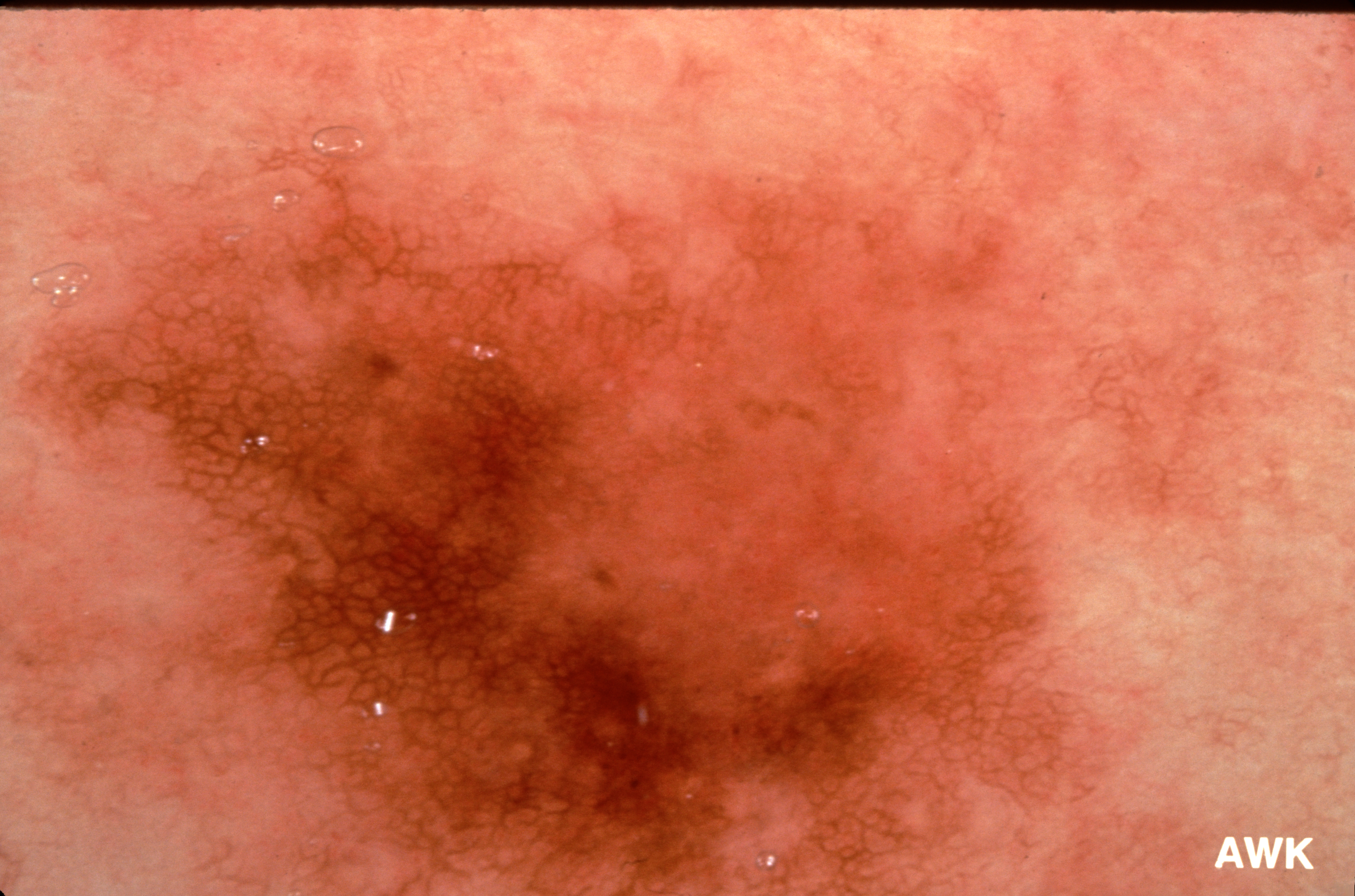A dermatoscopic image of a skin lesion.
The patient is a female about 55 years old.
Dermoscopic review identifies milia-like cysts and pigment network.
The lesion occupies roughly 47% of the field.
In (x1, y1, x2, y2) order, the visible lesion spans (53, 175, 1079, 895).
The biopsy diagnosis was a melanoma.